A female subject approximately 30 years of age; a dermoscopic image of a skin lesion.
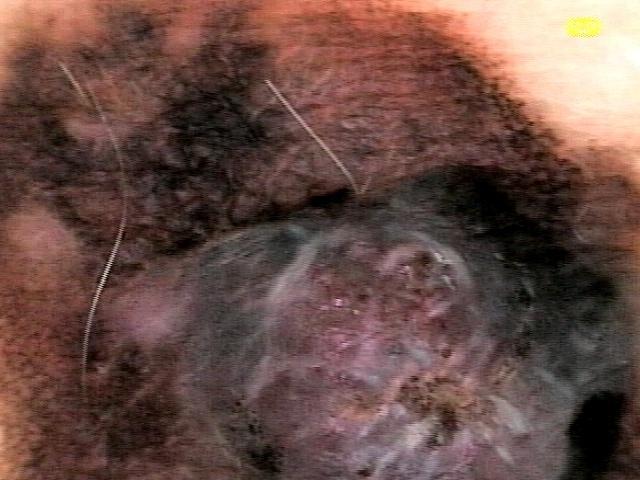| field | value |
|---|---|
| diagnostic label | Melanoma (biopsy-proven) |